A dermoscopic image of a skin lesion: 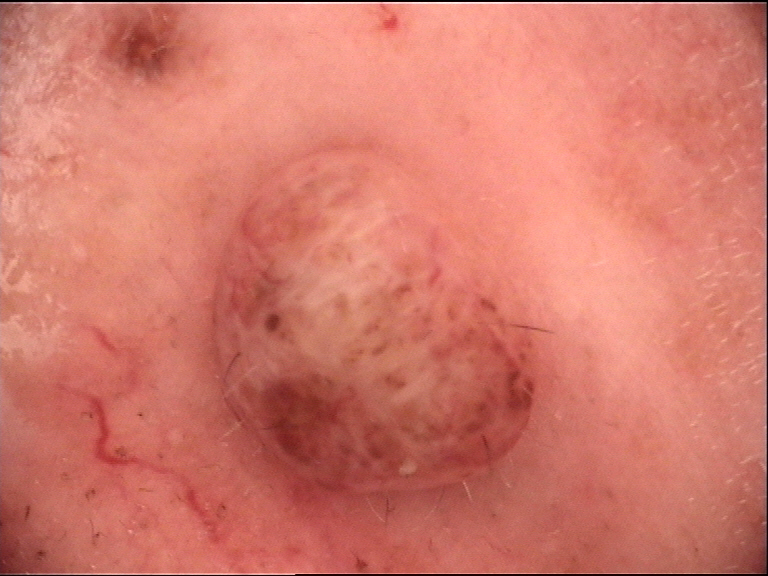Conclusion:
Consistent with a banal lesion — a dermal nevus.